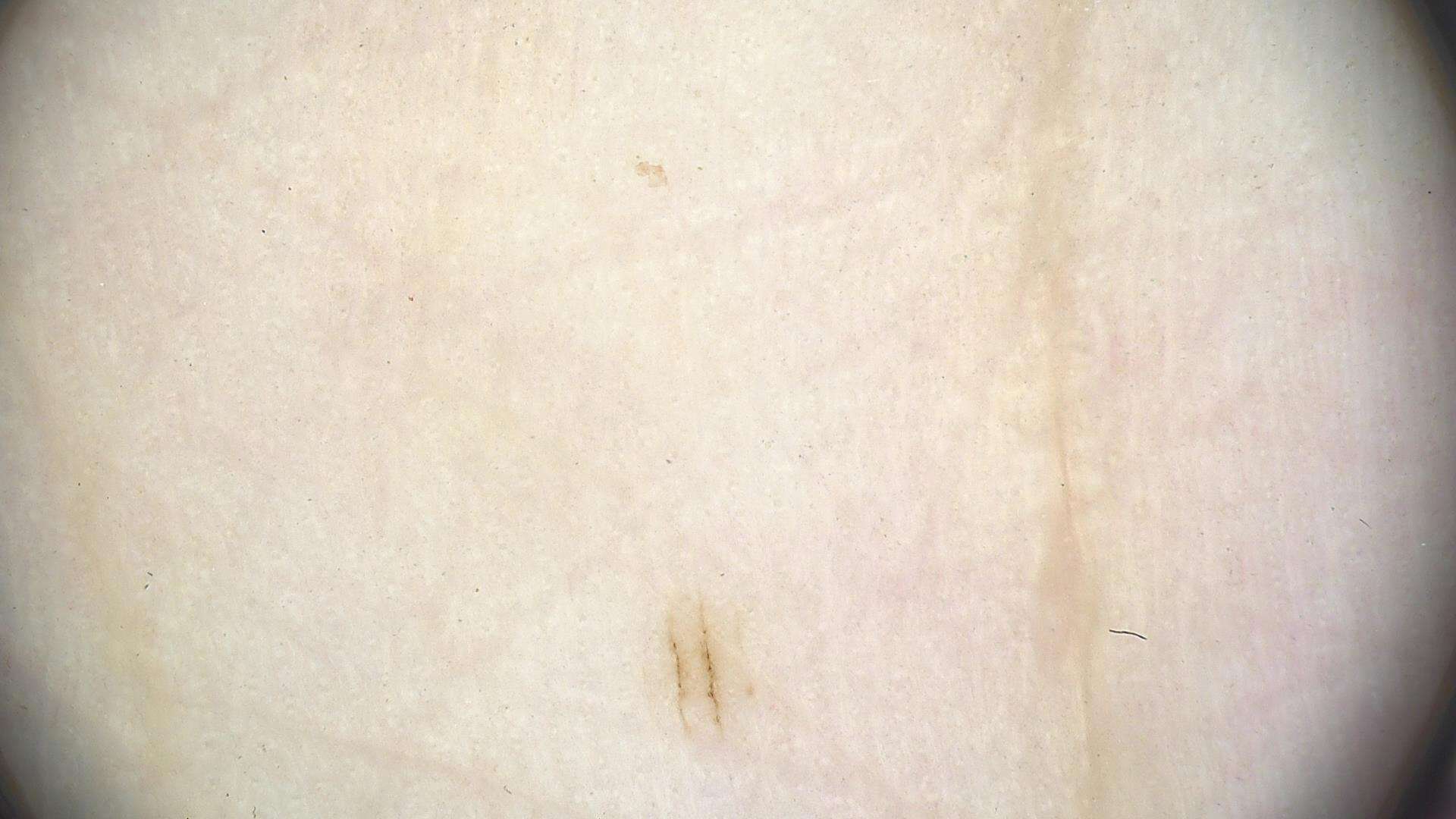{"image": "dermatoscopy", "diagnosis": {"name": "acral junctional nevus", "code": "ajb", "malignancy": "benign", "super_class": "melanocytic", "confirmation": "expert consensus"}}